Imaged for a research study, with no referral diagnosis recorded. The patient describes having numerous moles. Dermoscopy of a skin lesion. The patient reports a history of sunbed use and no immunosuppression. A female patient 26 years old:
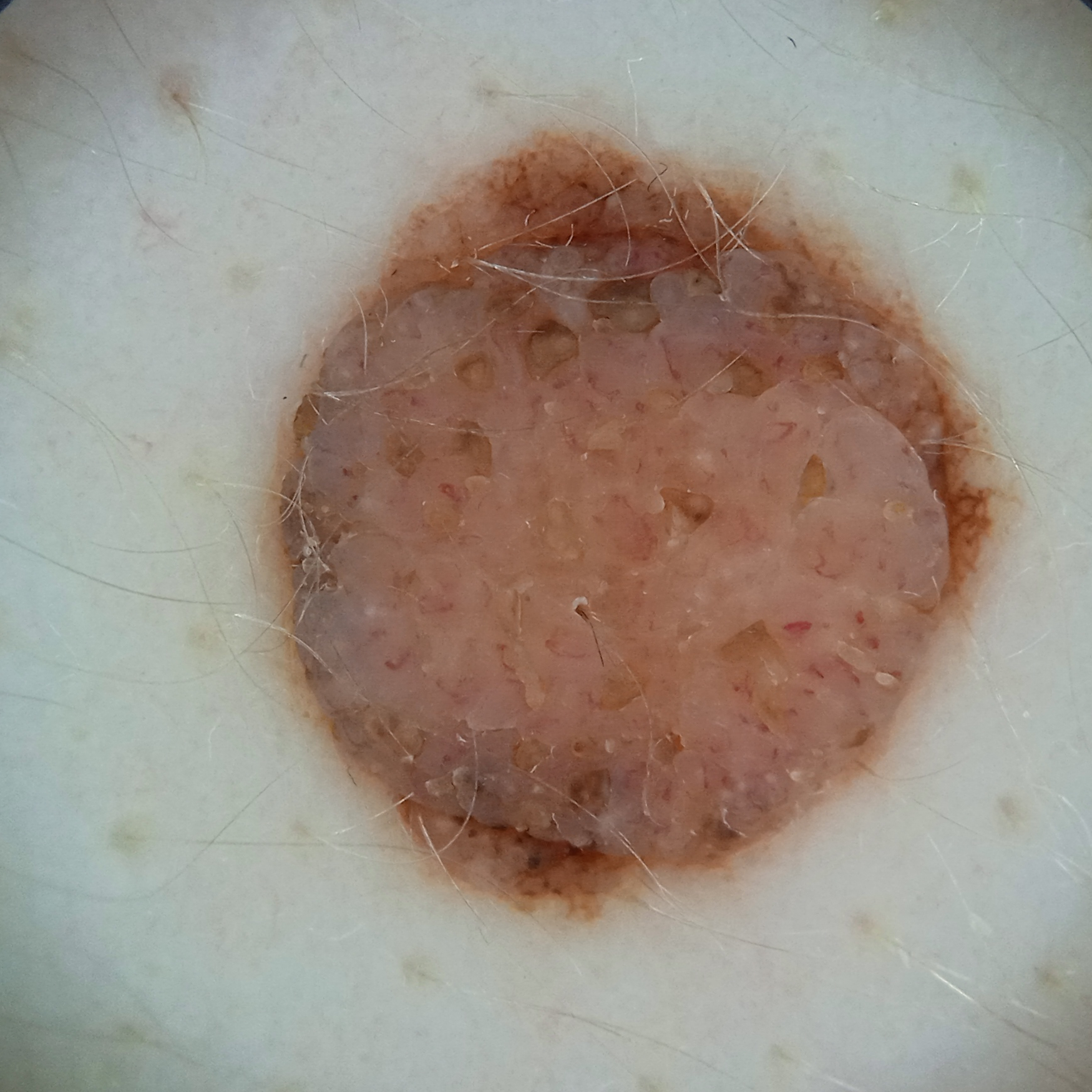Clinical context: Located on the back. Measuring roughly 8.9 mm. Conclusion: On independent review by four dermatologists, the agreed diagnosis was a melanocytic nevus.